The head or neck is involved · the patient reported no systemic symptoms · symptoms reported: itching, burning and pain · the patient described the issue as a rash · the photo was captured at an angle — 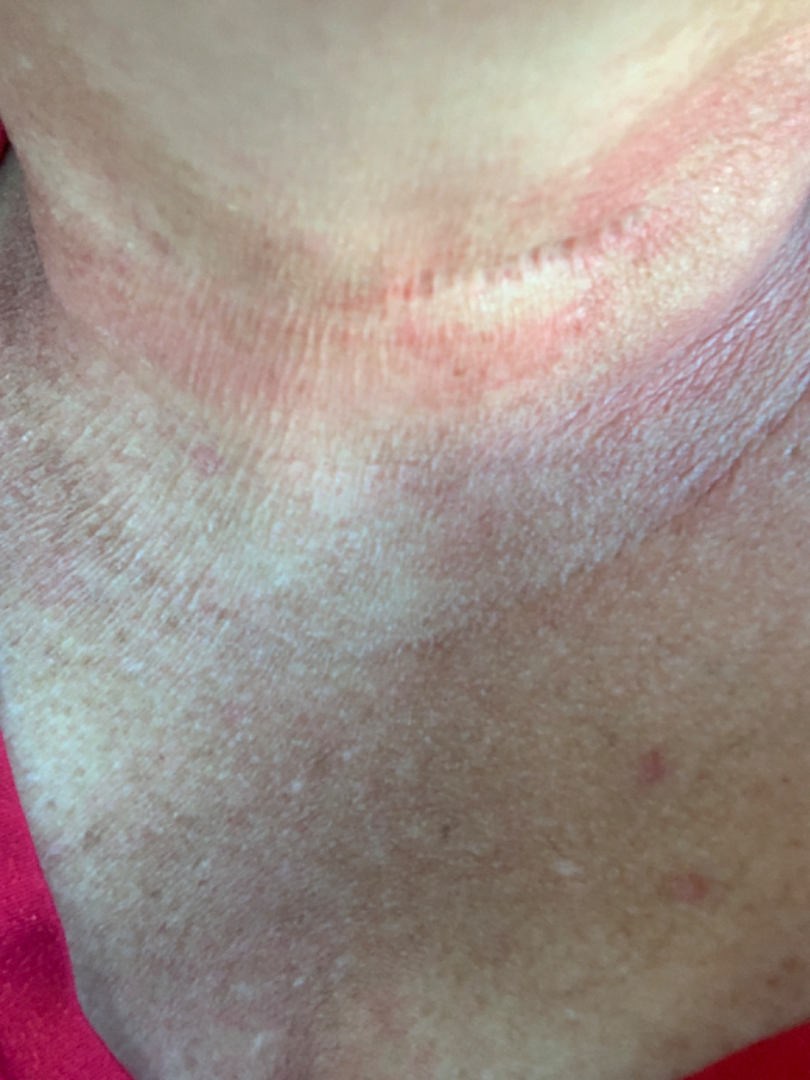  differential:
    tied_lead:
      - Photocontact dermatitis [berloque dermatitis]
      - Allergic Contact Dermatitis
      - Irritant Contact Dermatitis